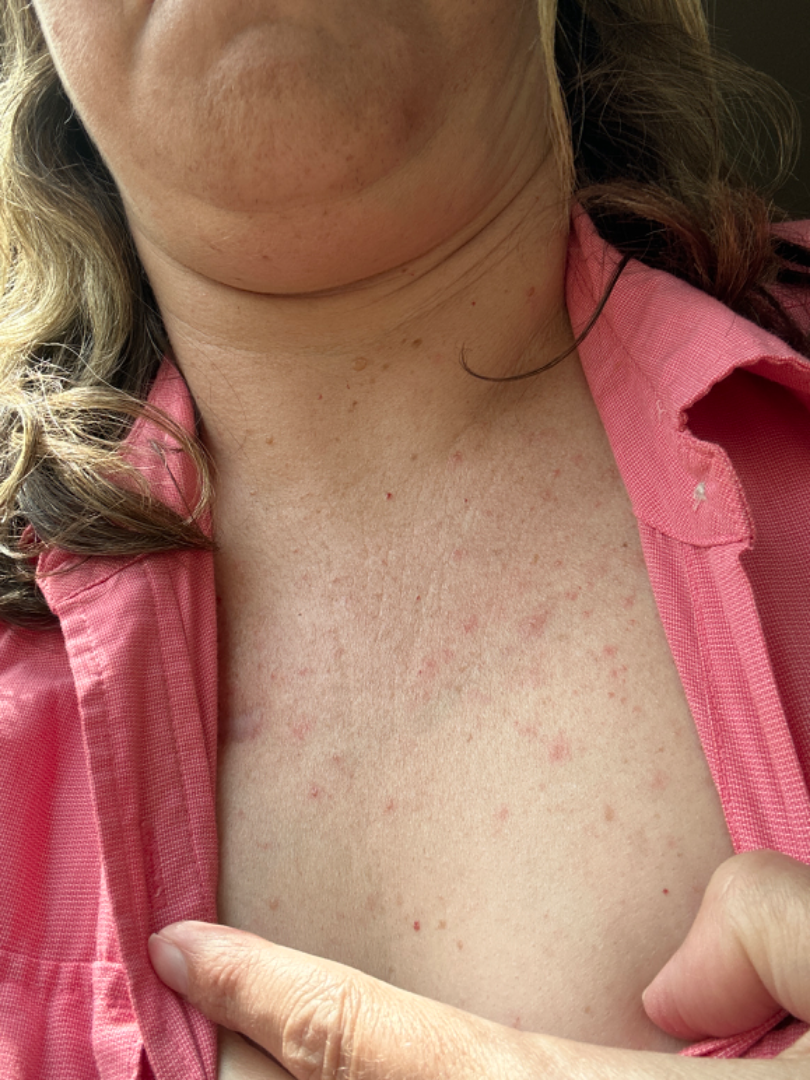Patient information: This image was taken at an angle. Review: Acne and Folliculitis were considered with similar weight; lower on the differential is Grover's disease.